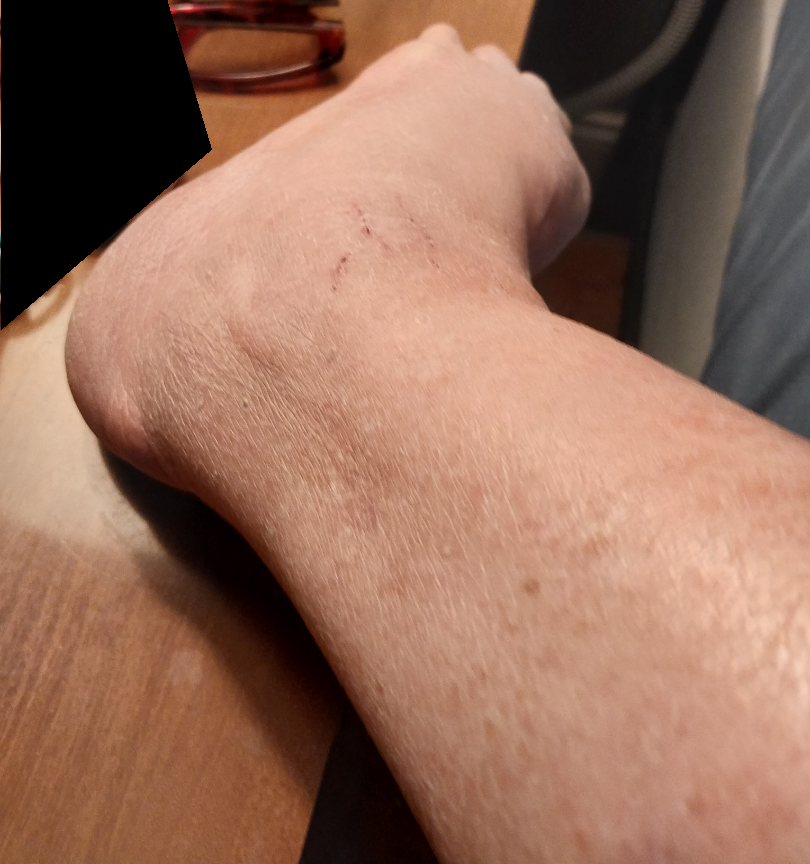site = top or side of the foot | image framing = at a distance | assessment = a single dermatologist reviewed the case: the primary impression is Eczema; possibly Xerosis.